A dermoscopy image of a skin lesion. A female patient aged 58. Collected as part of a research study, without a referral diagnosis. The patient says their skin tans without first burning. On a questionnaire the patient reported a personal history of skin cancer, a personal history of cancer, a family history of skin cancer, and no sunbed use: 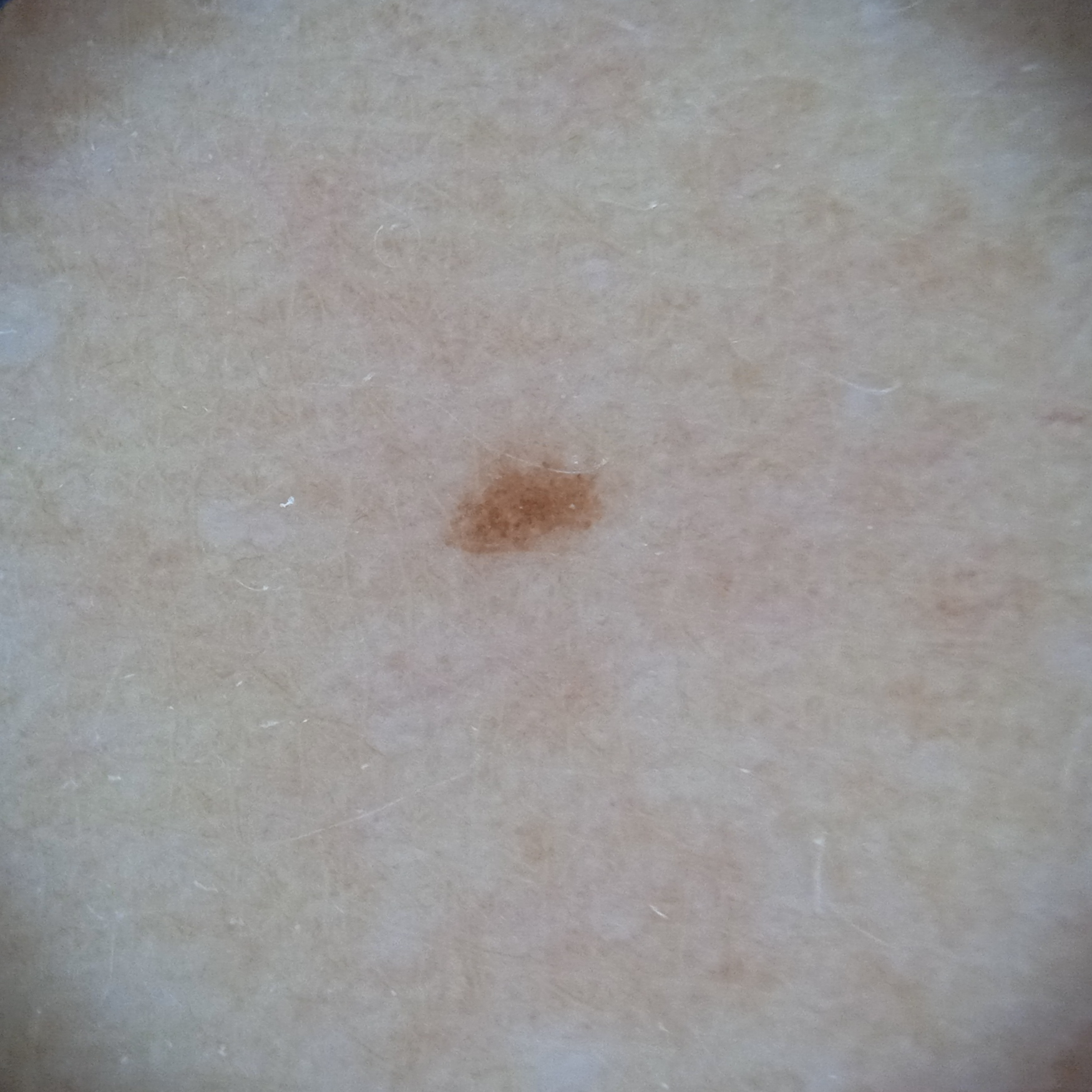site: an arm
lesion size: 1.9 mm
diagnosis: melanocytic nevus (dermatologist consensus)